This is a close-up image:
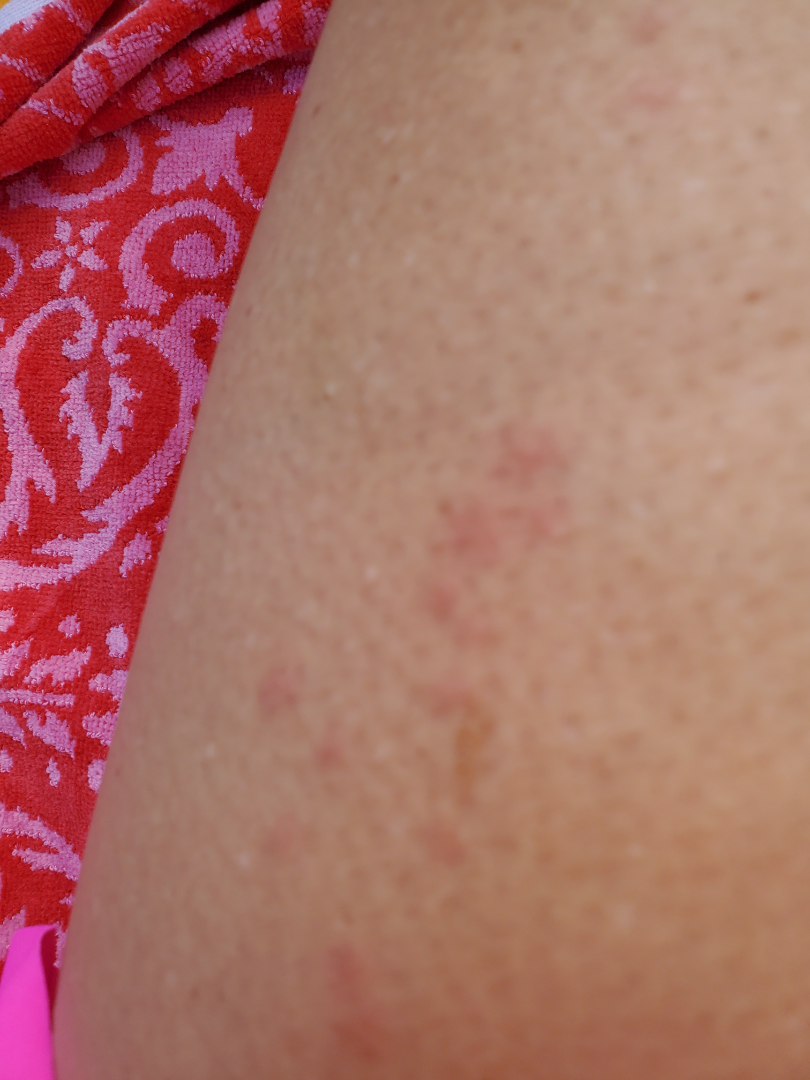| field | value |
|---|---|
| assessment | not assessable |